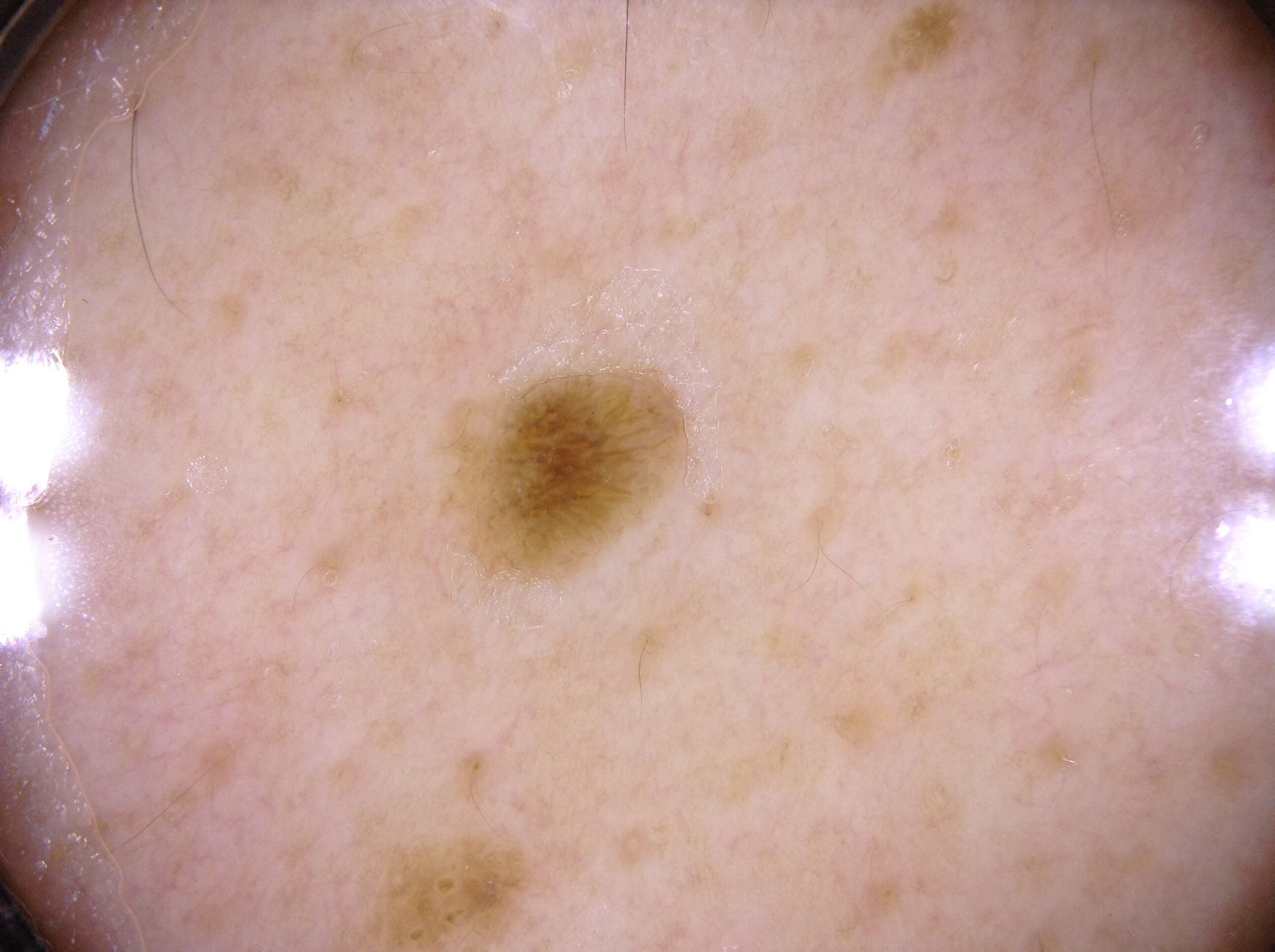patient = male, in their 60s
image = dermatoscopic image of a skin lesion
lesion size = ~2% of the field
lesion bbox = [478, 380, 667, 565]
absent dermoscopic features = negative network, milia-like cysts, pigment network, and streaks
diagnostic label = a seborrheic keratosis, a keratinocytic lesion